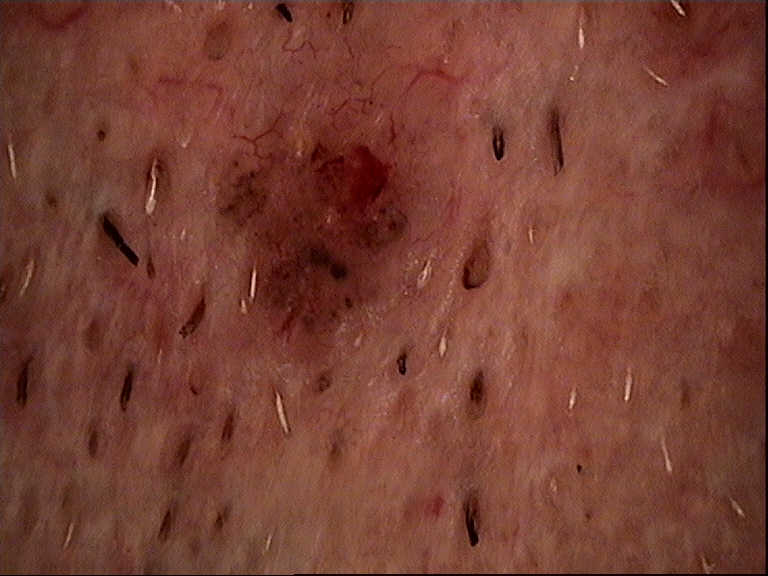A dermoscopy image of a single skin lesion. The morphology is that of a keratinocytic lesion. Histopathologically confirmed as a malignant lesion — a squamous cell carcinoma.